The leg is involved. The photo was captured at a distance. Female patient, age 18–29 — 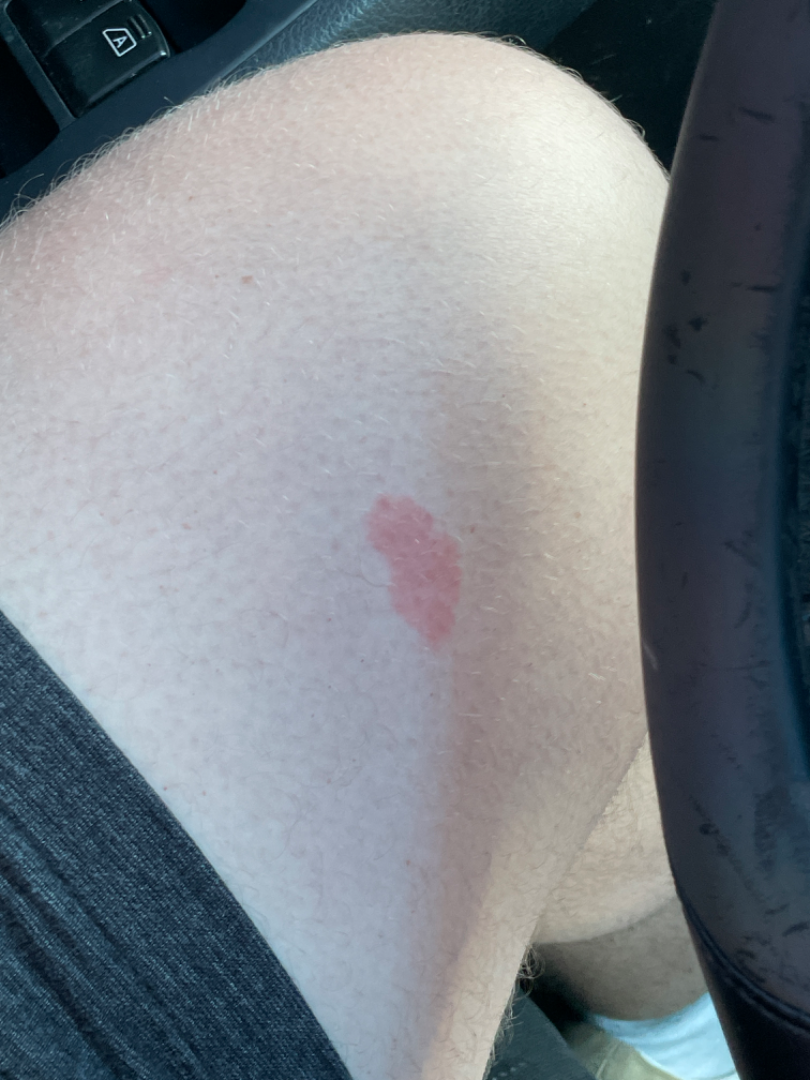The skin findings could not be characterized from the image.